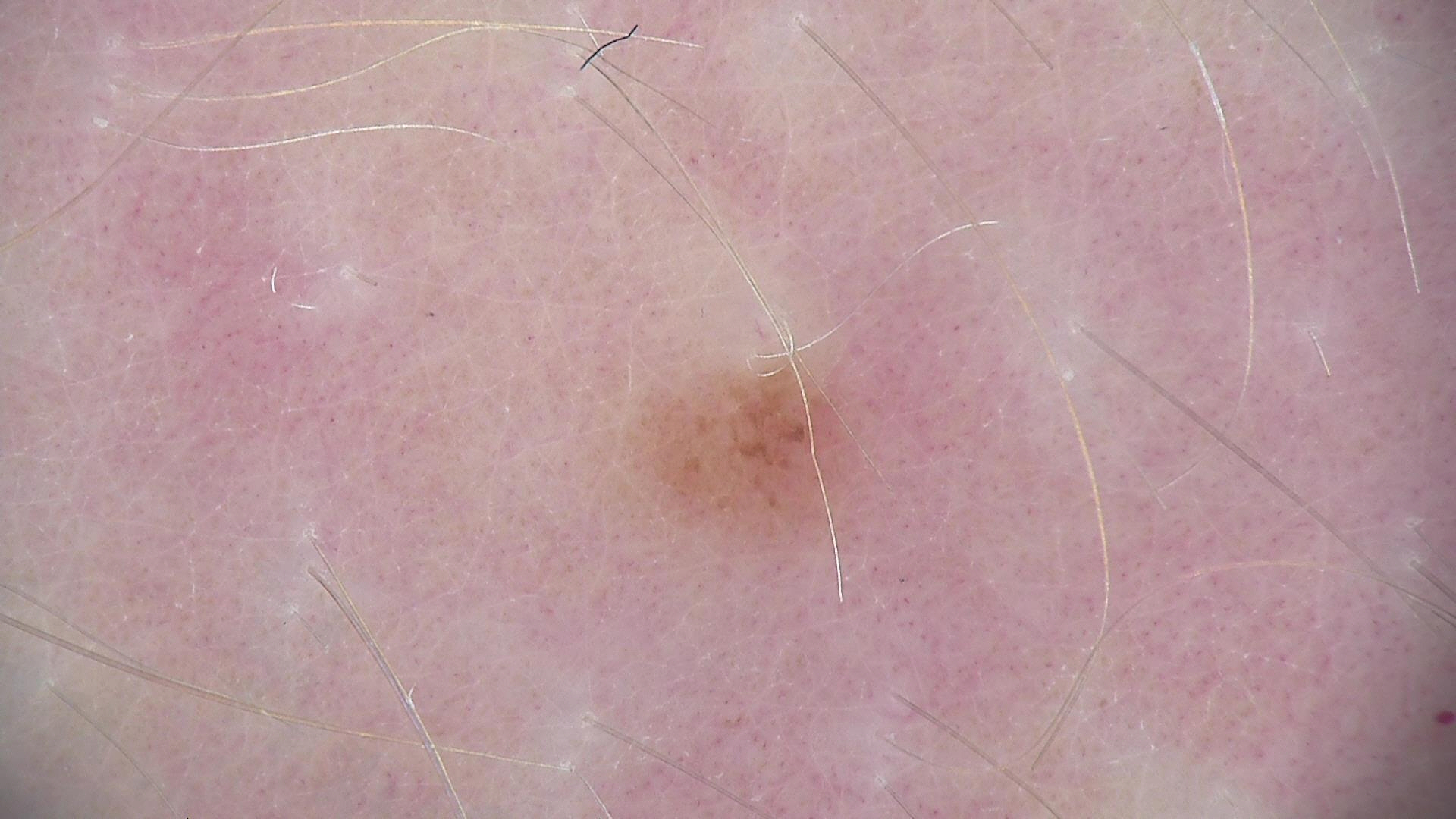Classified as a compound nevus.